A dermatoscopic image of a skin lesion: 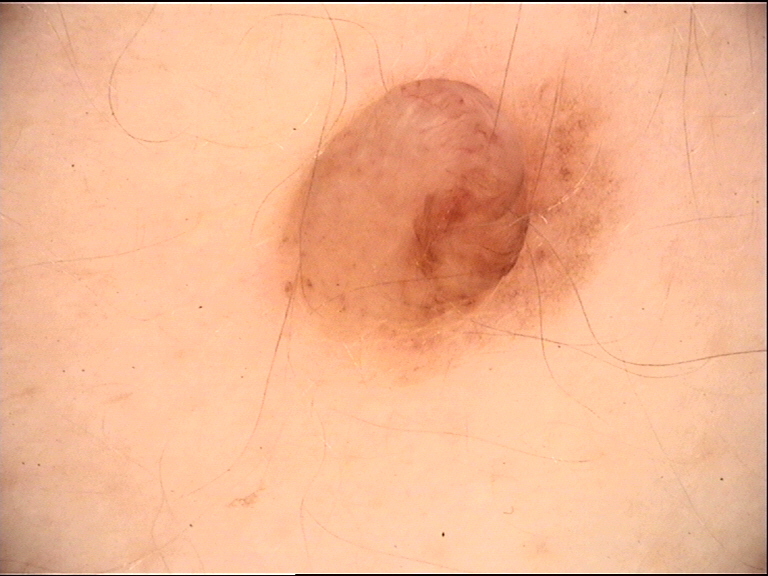lesion_type:
  main_class: banal
  pattern: dermal
diagnosis:
  name: dermal nevus
  code: db
  malignancy: benign
  super_class: melanocytic
  confirmation: expert consensus